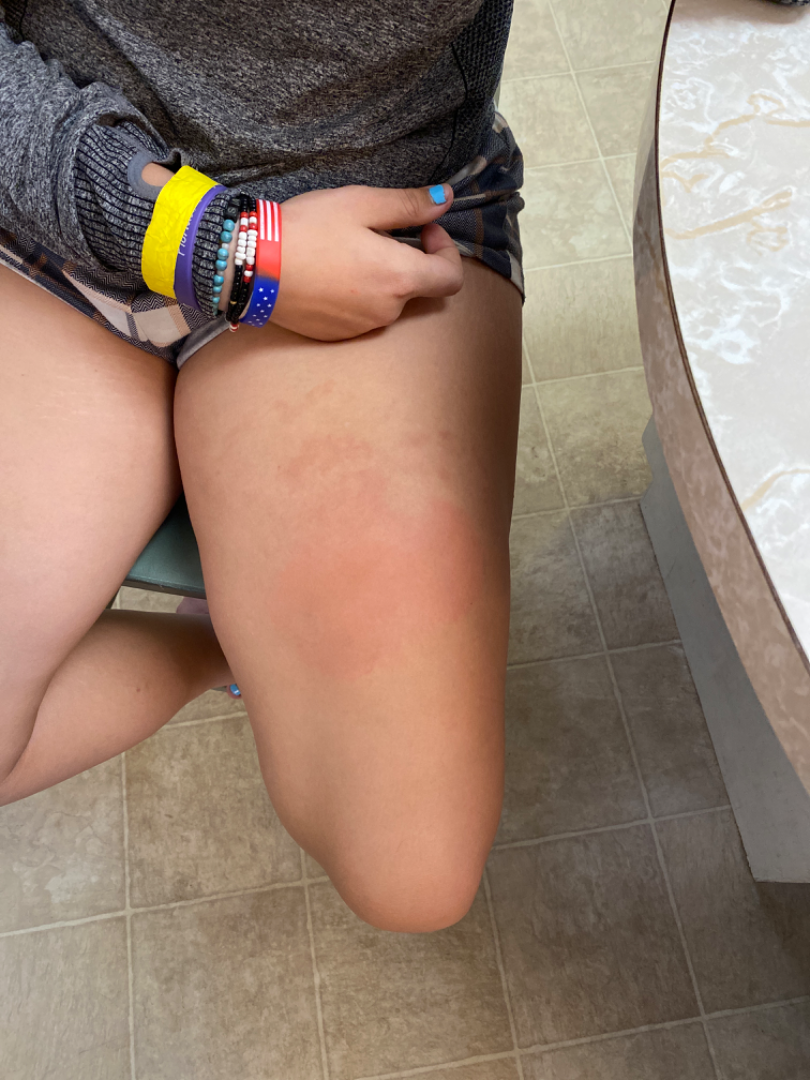Background:
Texture is reported as raised or bumpy. The lesion is associated with itching and enlargement. This image was taken at a distance. Self-categorized by the patient as a rash. The condition has been present for one to four weeks. Skin tone: Fitzpatrick III; lay reviewers estimated a Monk Skin Tone of 3. Located on the leg. The contributor is a female aged 18–29.
Findings:
The reviewing dermatologist's impression was: most likely Hypersensitivity; with consideration of Urticaria.